The lesion is associated with itching · reported duration is about one day · an image taken at a distance · the subject is a female aged 50–59 · self-categorized by the patient as a rash · associated systemic symptoms include fever · the lesion is described as raised or bumpy · skin tone: FST III · the lesion involves the arm:
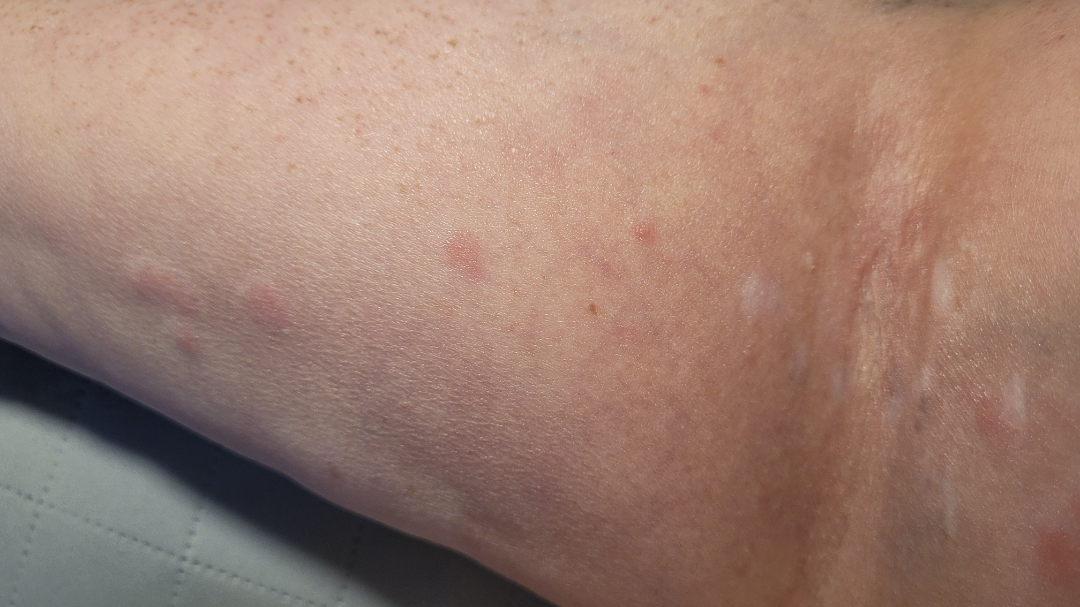Q: What is the differential diagnosis?
A: Eczema, Allergic Contact Dermatitis, Urticaria and Insect Bite were each considered, in no particular order